A skin lesion imaged with a dermatoscope — 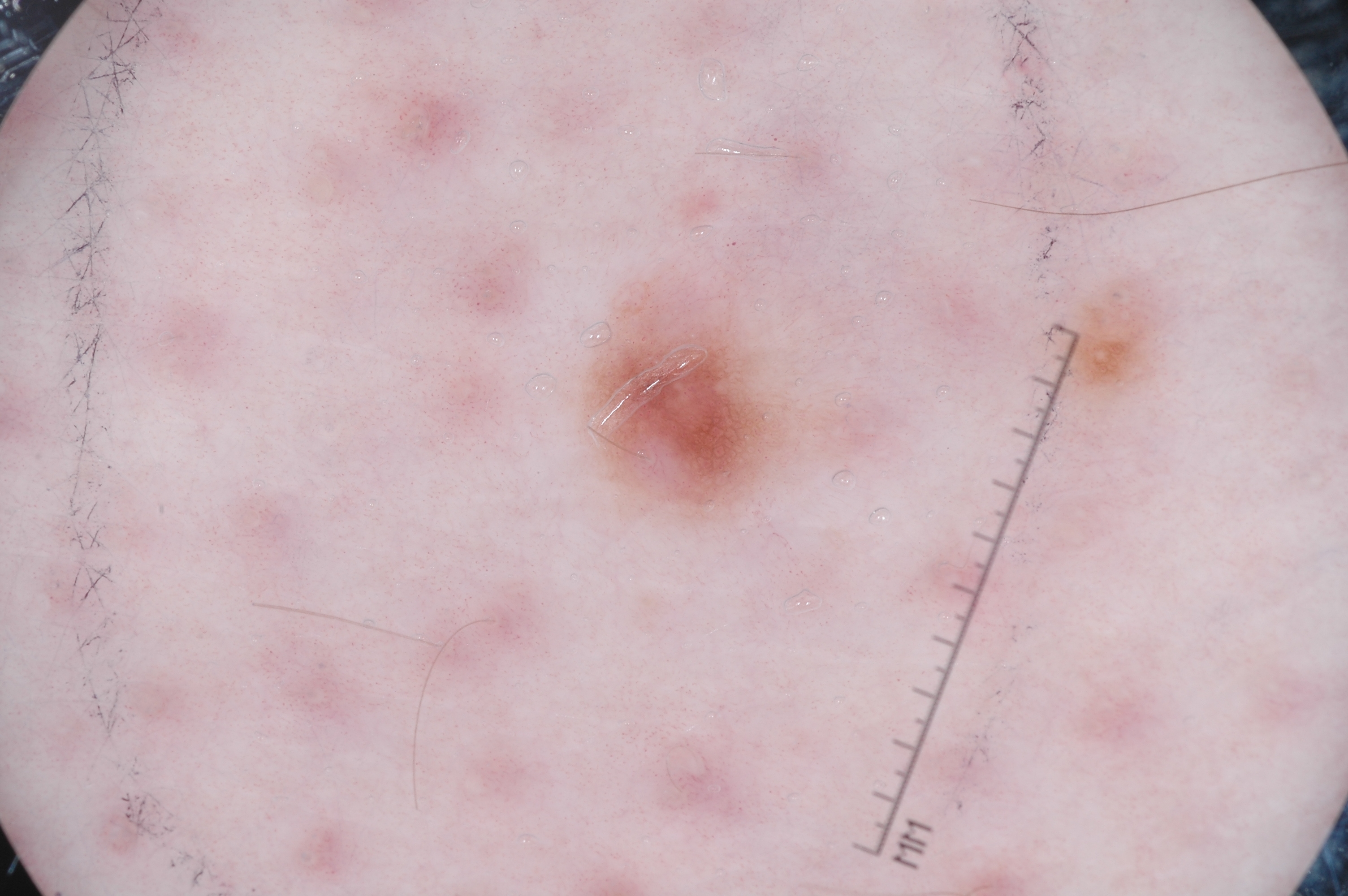{
  "lesion_location": {
    "bbox_xyxy": [
      590,
      294,
      790,
      518
    ]
  },
  "diagnosis": {
    "name": "melanocytic nevus",
    "malignancy": "benign",
    "lineage": "melanocytic",
    "provenance": "clinical"
  }
}